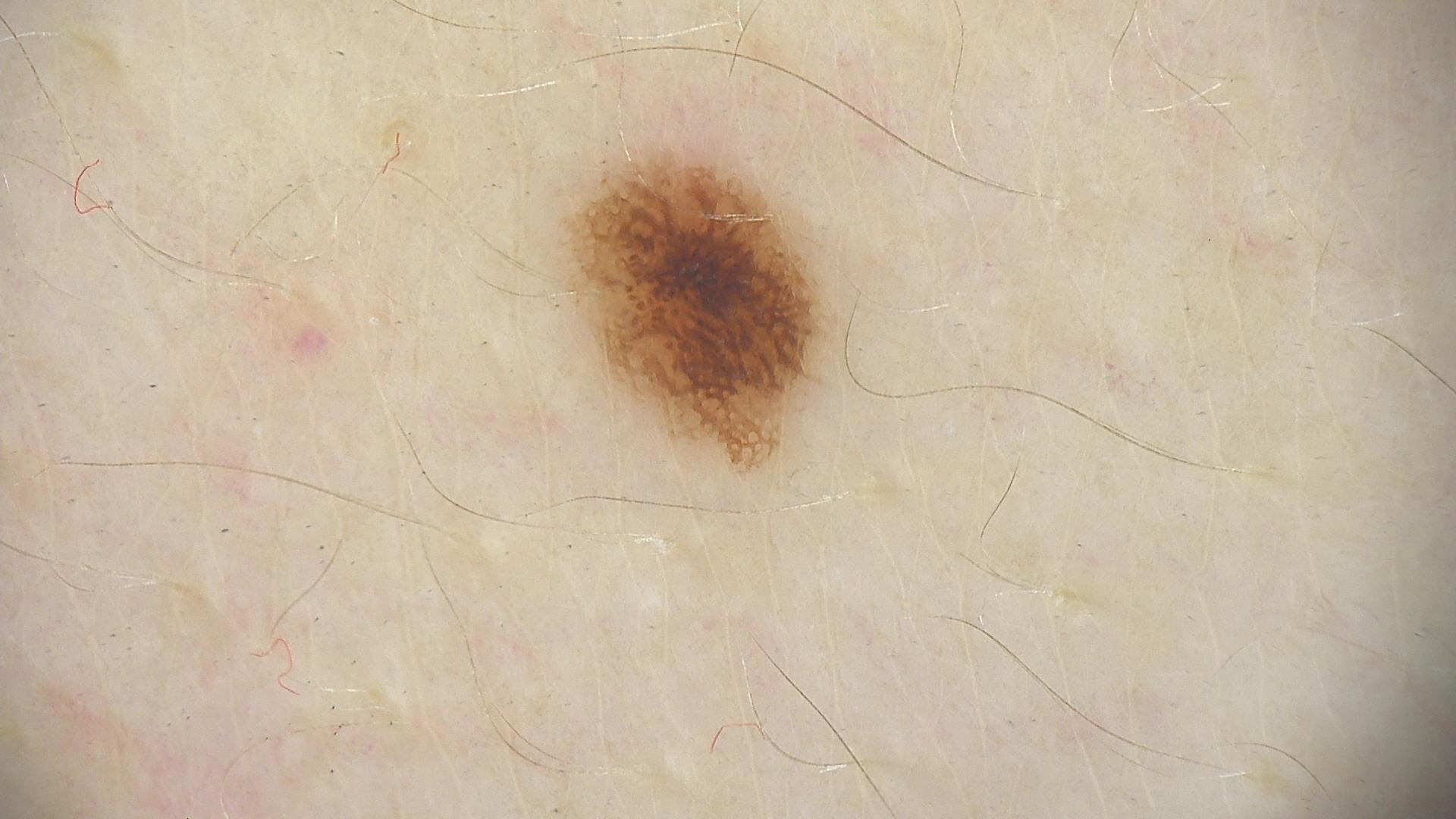Q: What kind of image is this?
A: dermatoscopy
Q: What was the diagnostic impression?
A: dysplastic junctional nevus (expert consensus)